A dermoscopic photograph of a skin lesion: 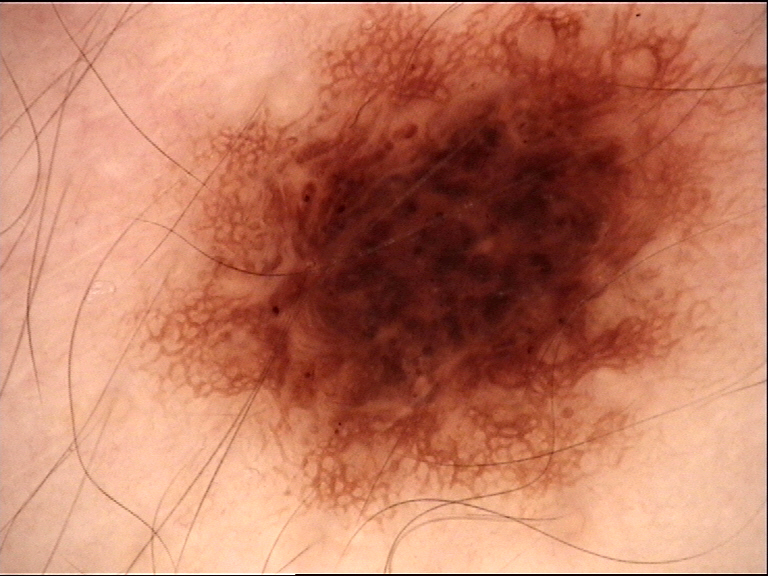Impression:
Classified as a benign lesion — a dysplastic compound nevus.